Dermoscopy of a skin lesion.
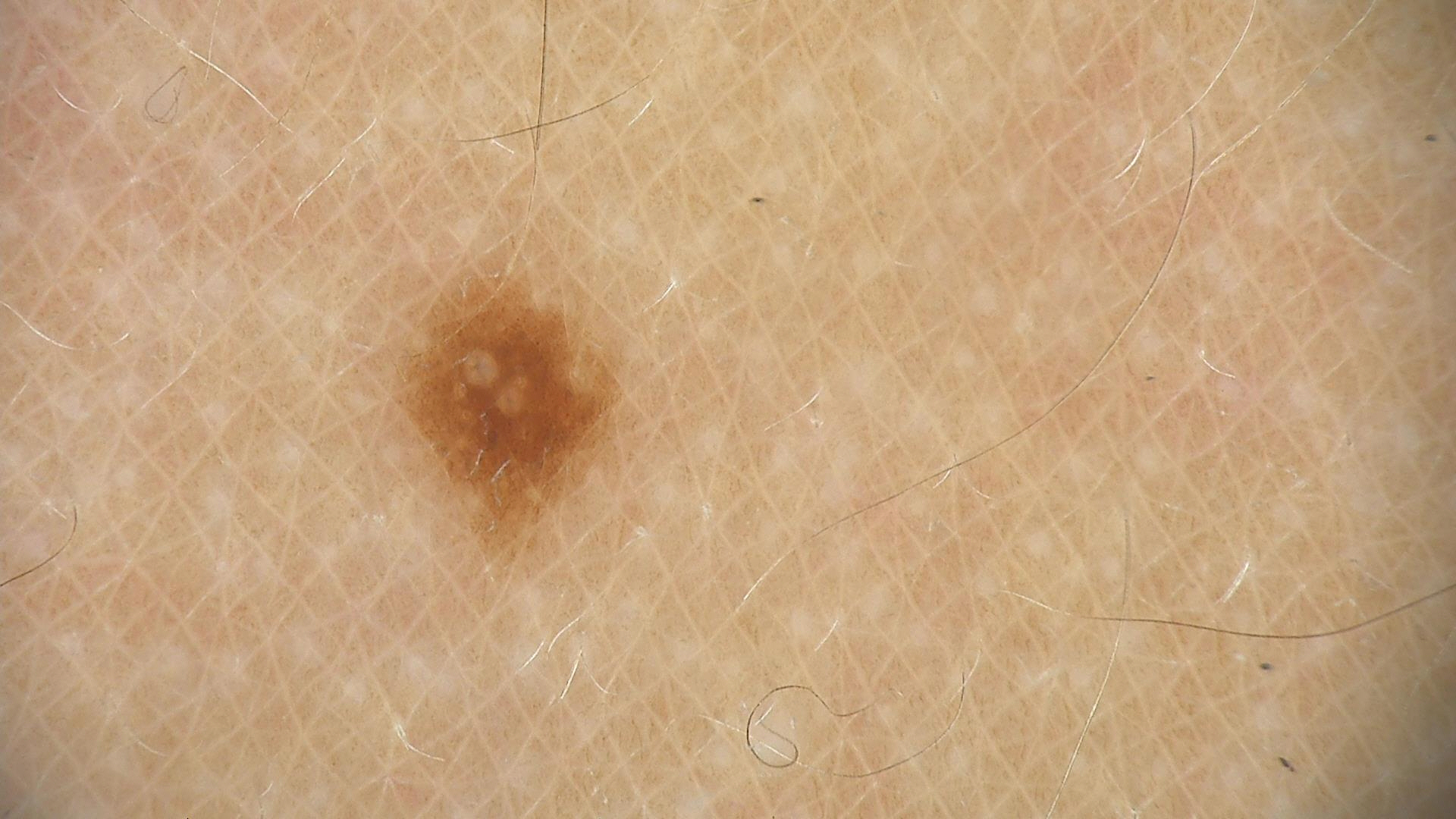  diagnosis:
    name: dysplastic junctional nevus
    code: jd
    malignancy: benign
    super_class: melanocytic
    confirmation: expert consensus